A skin lesion imaged with a dermatoscope.
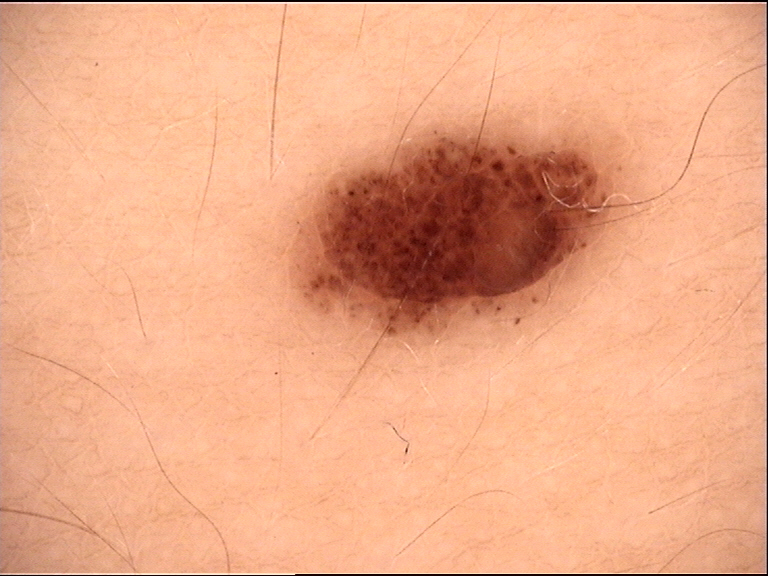This is a banal lesion. Consistent with a compound nevus.